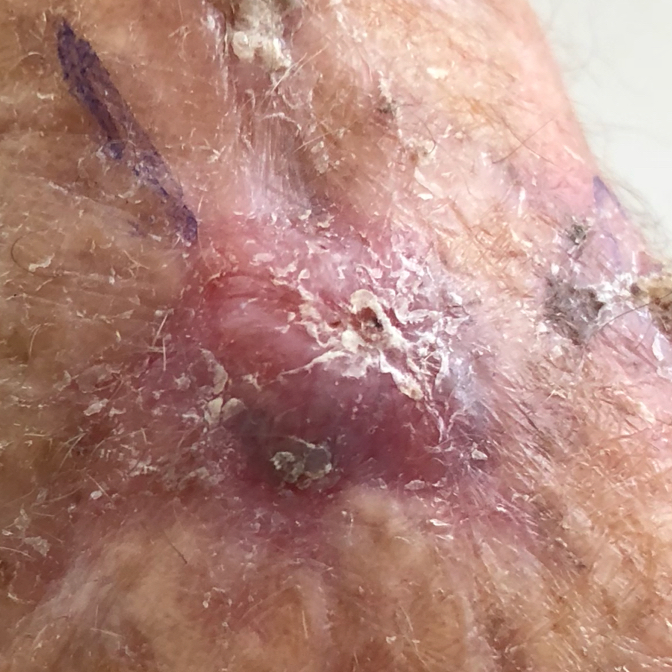{"patient": {"age": 79, "gender": "female"}, "lesion_location": "the nose", "symptoms": {"present": ["growth", "itching", "pain", "elevation"]}, "diagnosis": {"name": "basal cell carcinoma", "code": "BCC", "malignancy": "malignant", "confirmation": "histopathology"}}